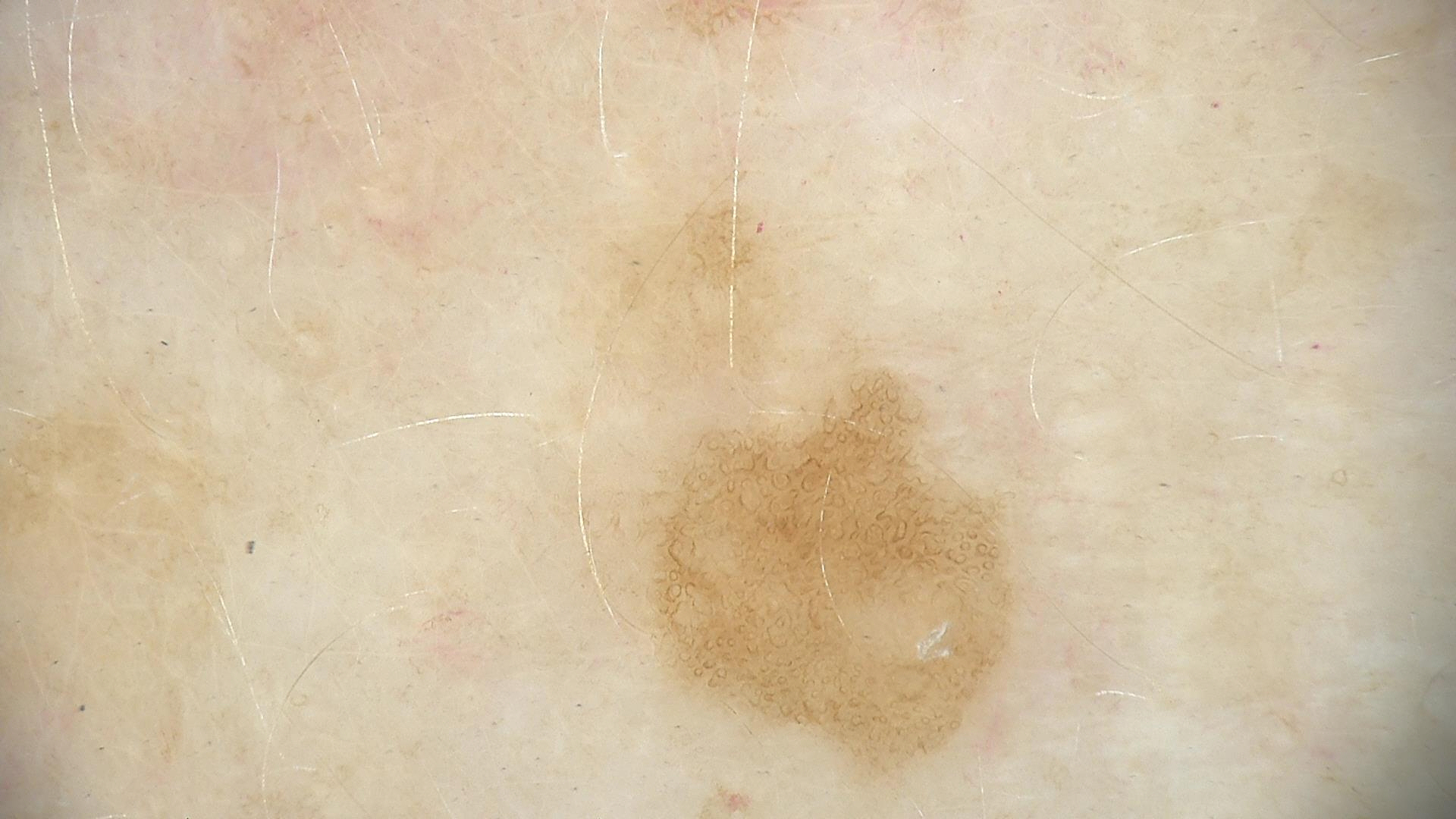Summary: A dermoscopic image of a skin lesion. The morphology is that of a keratinocytic lesion. Impression: Labeled as a seborrheic keratosis.